A clinical photograph of a skin lesion — 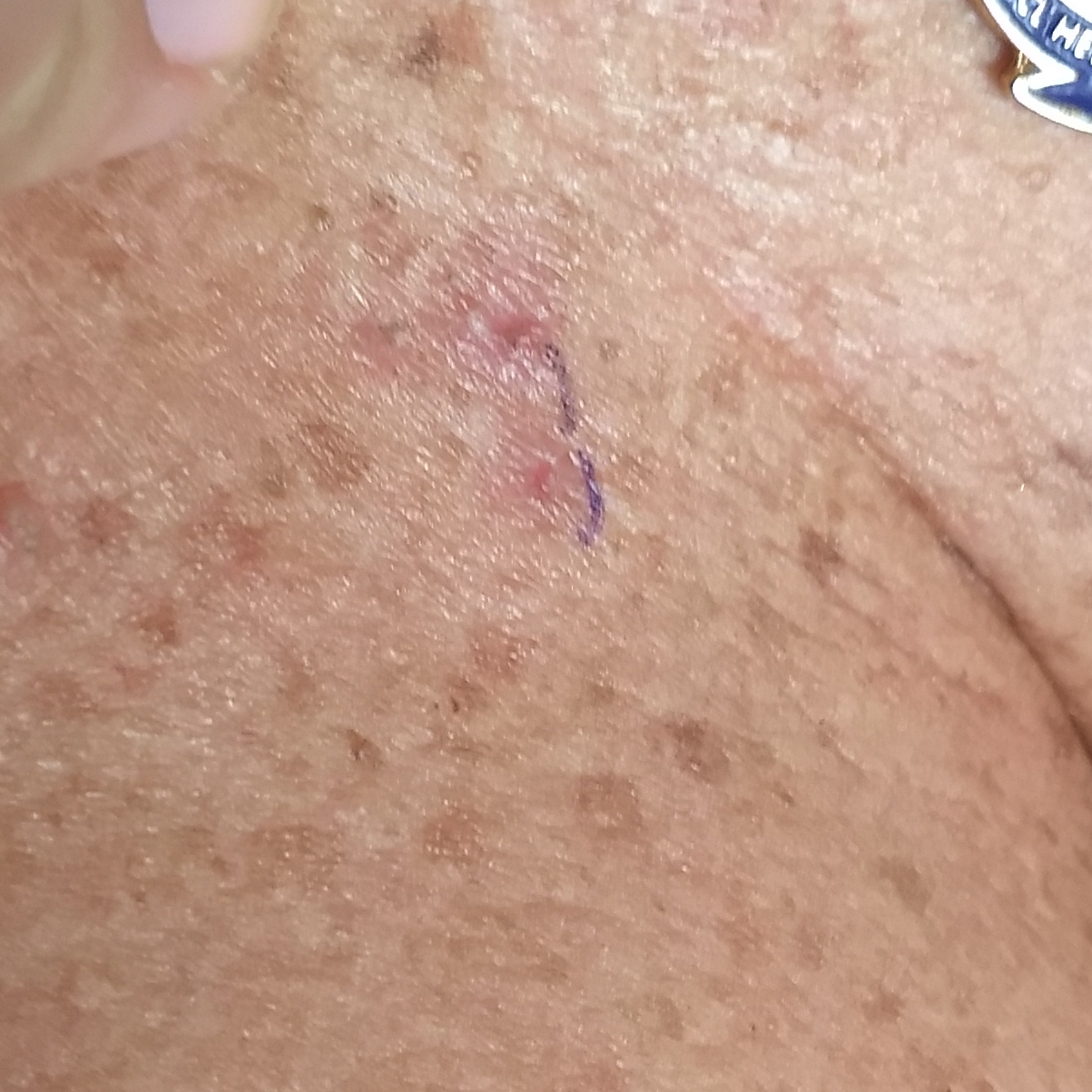Q: Where on the body is the lesion?
A: the chest
Q: Any reported symptoms?
A: itching
Q: What is the diagnosis?
A: actinic keratosis (clinical consensus)